A female patient 75 years of age. A moderate number of moles by the patient's own estimate. Collected as part of a research study, without a referral diagnosis. The patient reports a personal history of skin cancer and a personal history of cancer. A skin lesion imaged with a dermatoscope. The patient says their skin tans without first burning: 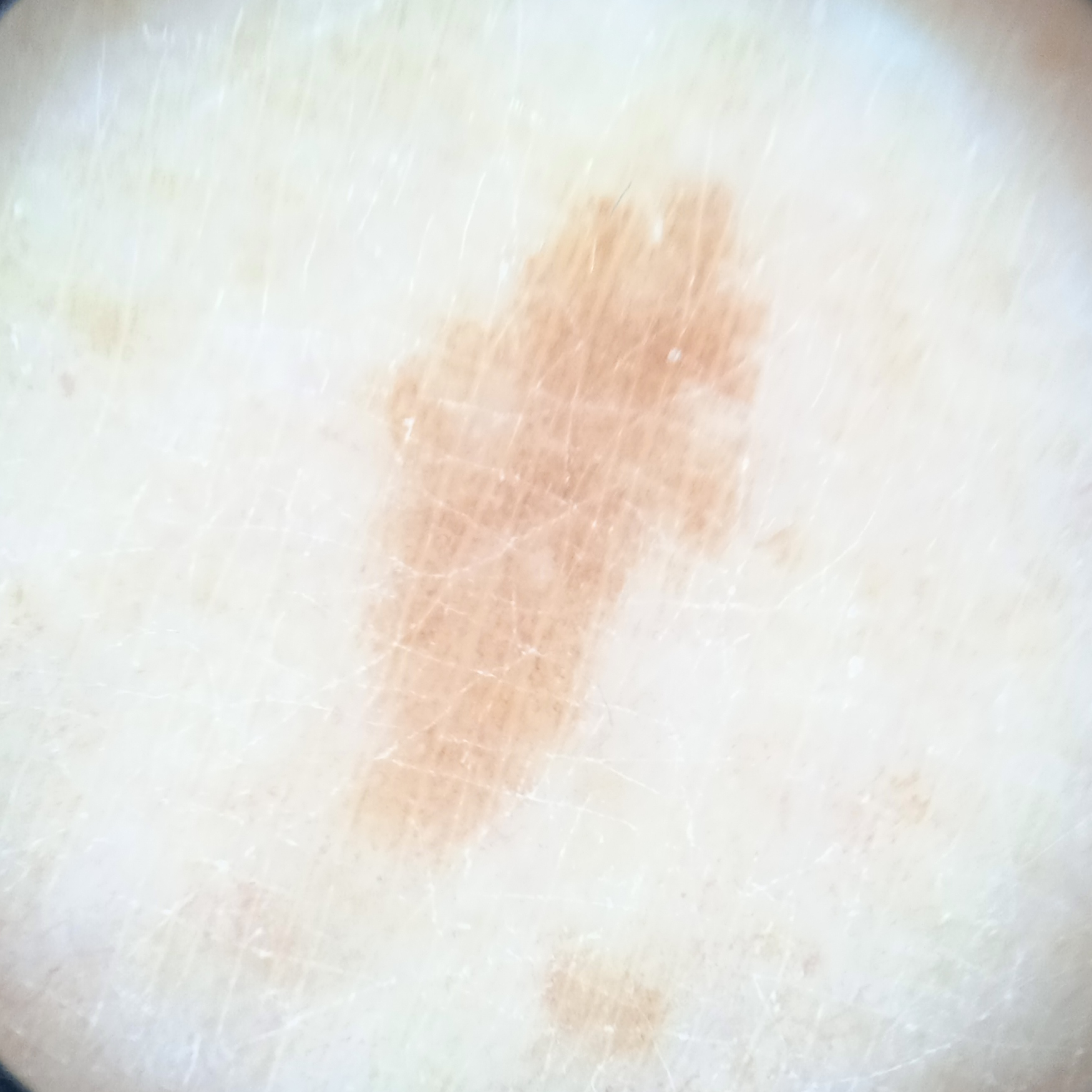body site = a leg
diagnostic label = melanocytic nevus (dermatologist consensus)